A dermoscopic close-up of a skin lesion, the subject is a female roughly 25 years of age: 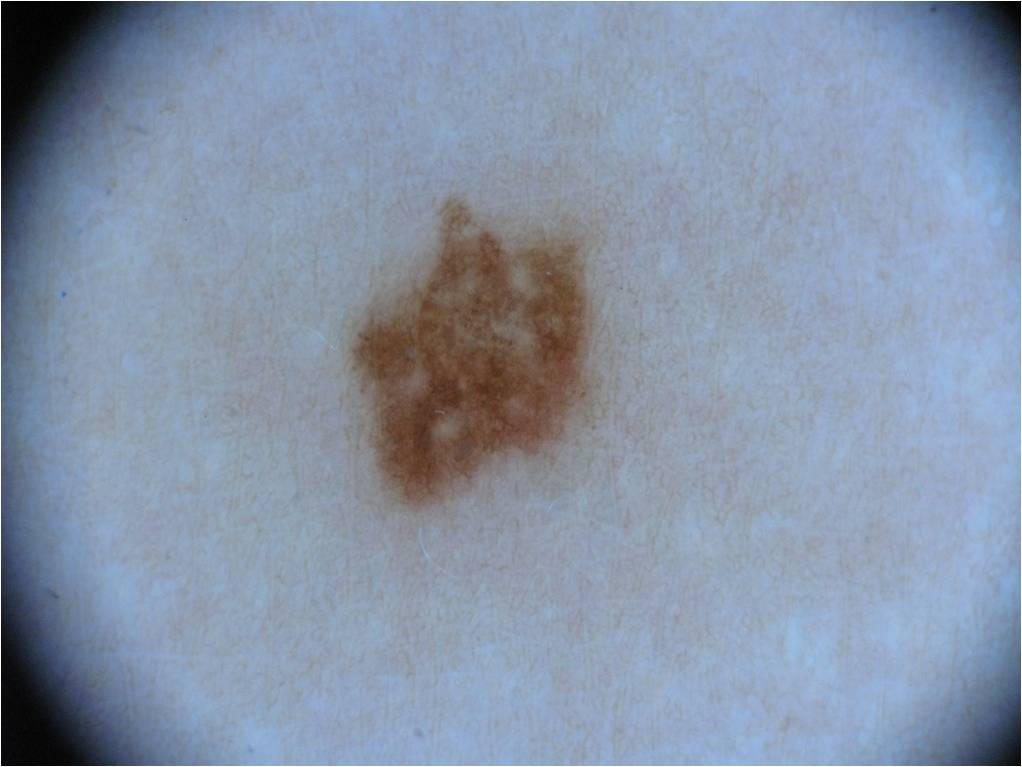dermoscopic features = pigment network and globules; absent: milia-like cysts, streaks, and negative network | lesion location = x1=335, y1=192, x2=618, y2=532 | lesion extent = ~9% of the field | diagnostic label = a melanocytic nevus.